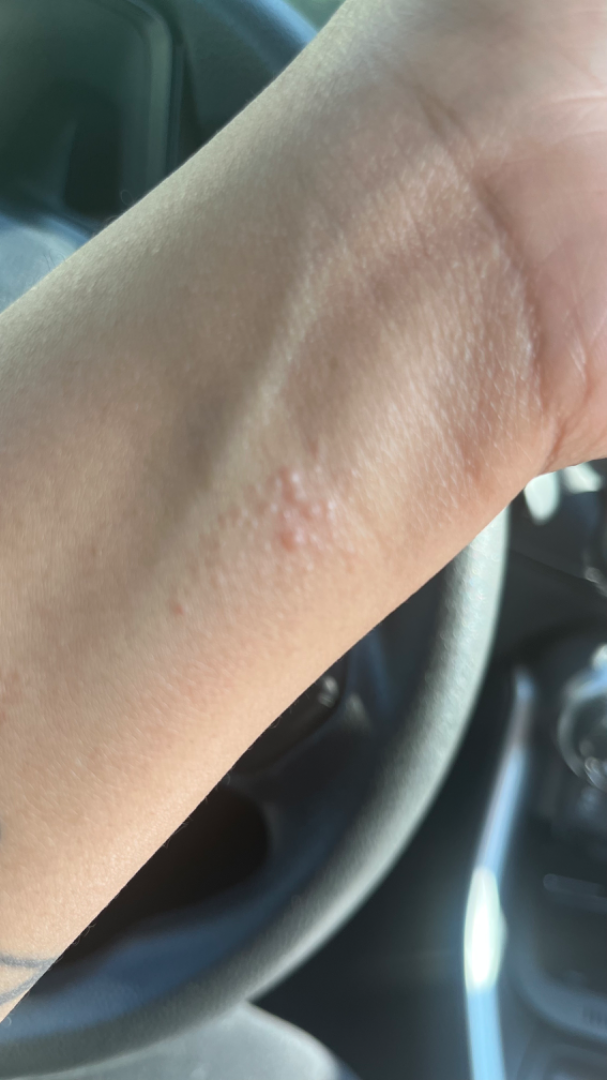History: The contributor reports itching, bothersome appearance, pain and enlargement. Female patient, age 18–29. The lesion is described as raised or bumpy. The condition has been present for about one day. Close-up view. The patient considered this a rash. The arm is involved. Impression: The leading consideration is Allergic Contact Dermatitis; also raised was Irritant Contact Dermatitis.